The contributor is a female aged 18–29, the photograph was taken at an angle, located on the leg.
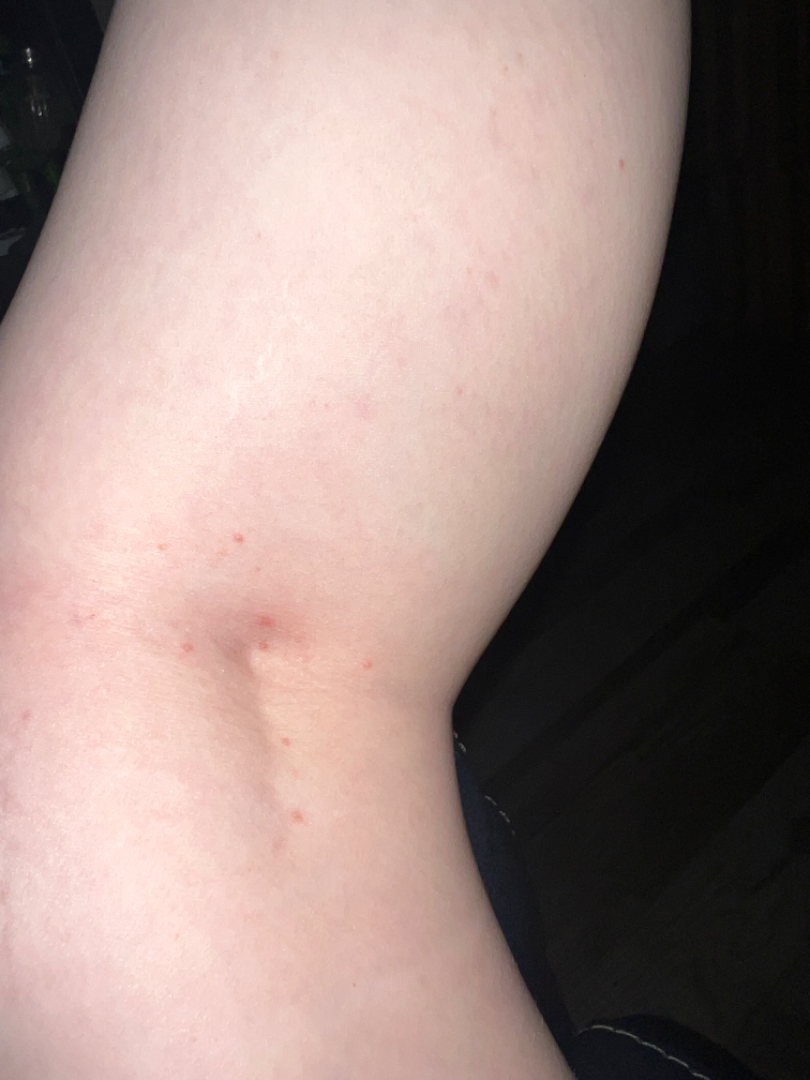patient's own categorization: a rash | duration: one to four weeks | reported symptoms: itching | lesion texture: raised or bumpy | differential: favoring Miliaria; possibly Folliculitis; with consideration of Molluscum Contagiosum; less likely is Irritant Contact Dermatitis.